The patient says their skin reddens with sun exposure. Imaged for a research study, with no referral diagnosis recorded:
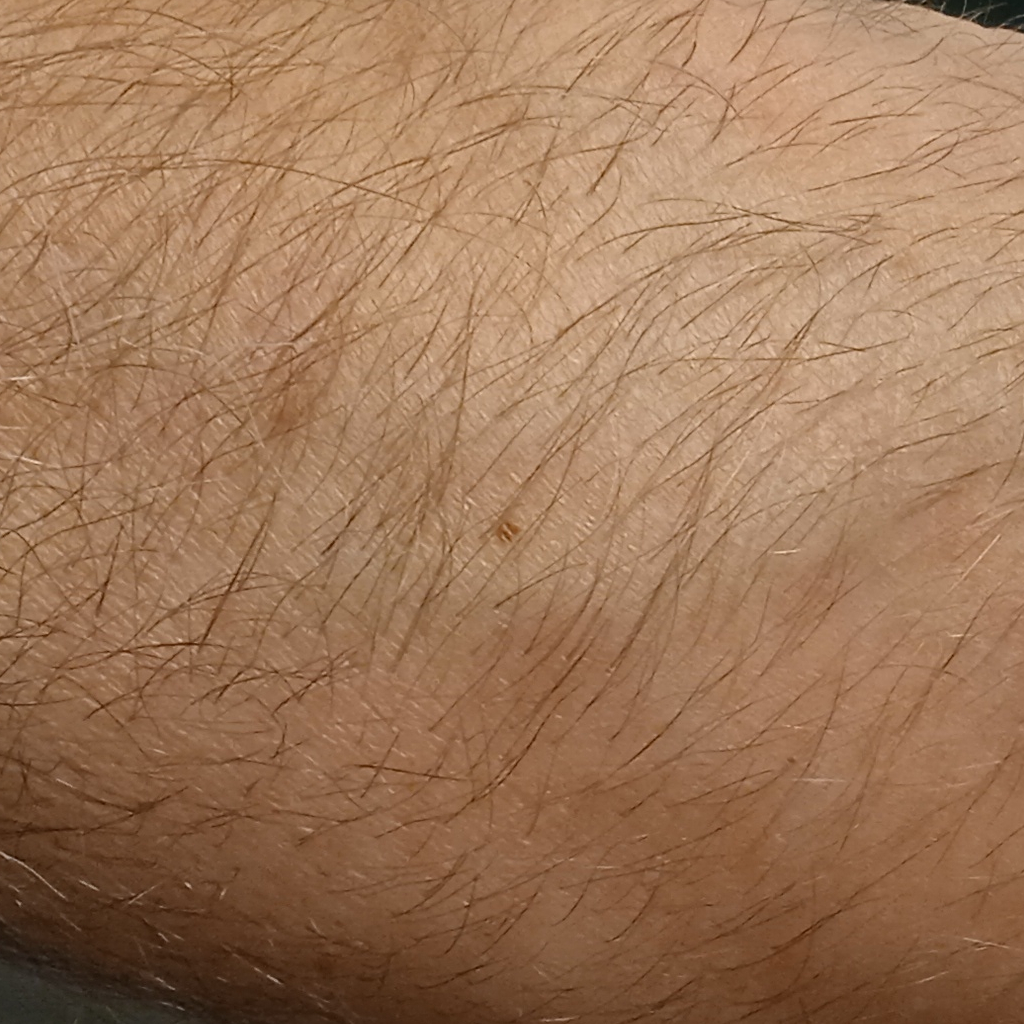- body site · an arm
- size · 1.5 mm
- diagnostic label · melanocytic nevus (dermatologist consensus)